A contact-polarized dermoscopy image of a skin lesion. The patient is skin type II.
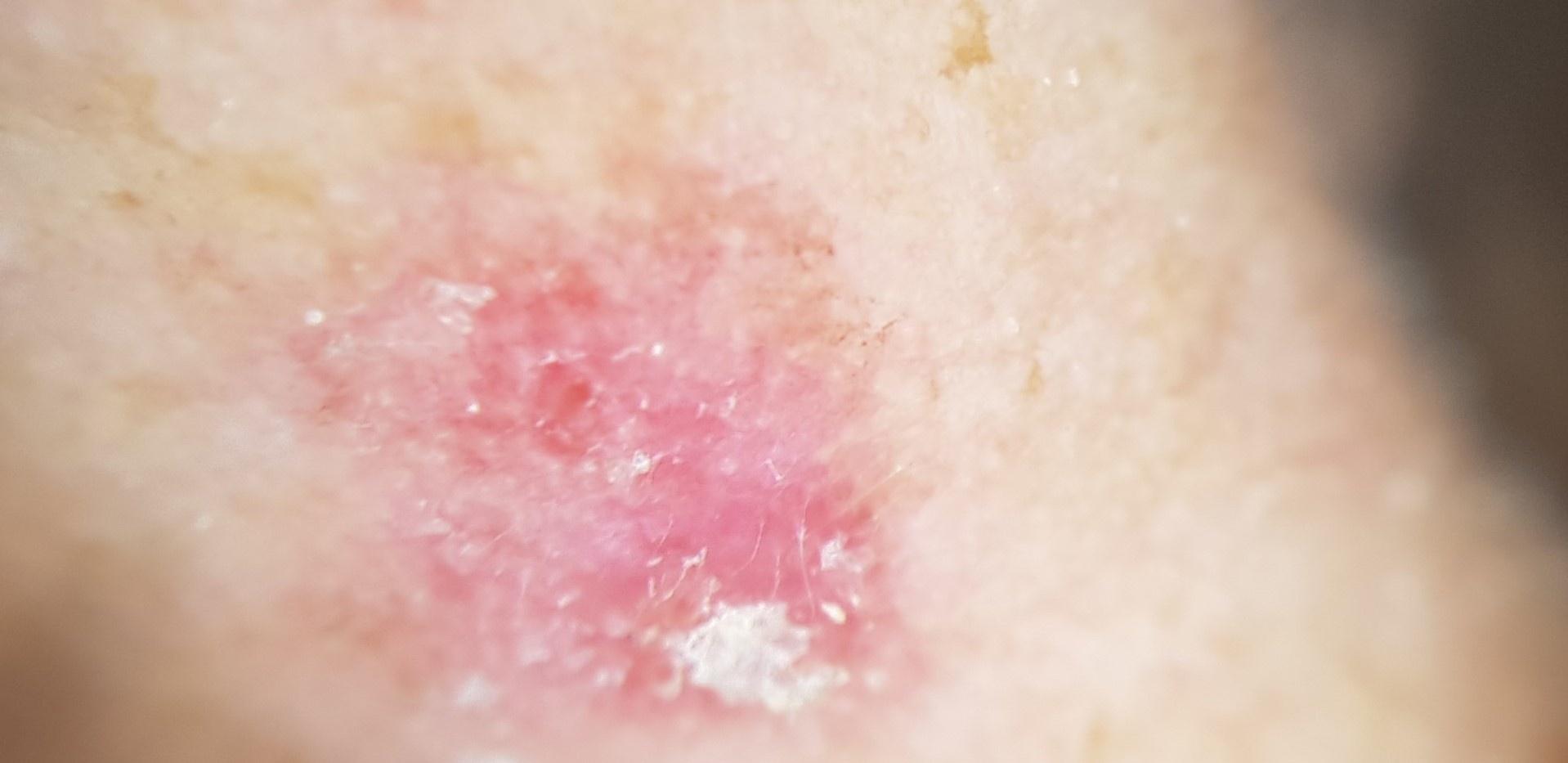diagnosis — Solar or actinic keratosis (biopsy-proven)